The arm is involved; close-up view; the patient is a female aged 40–49: 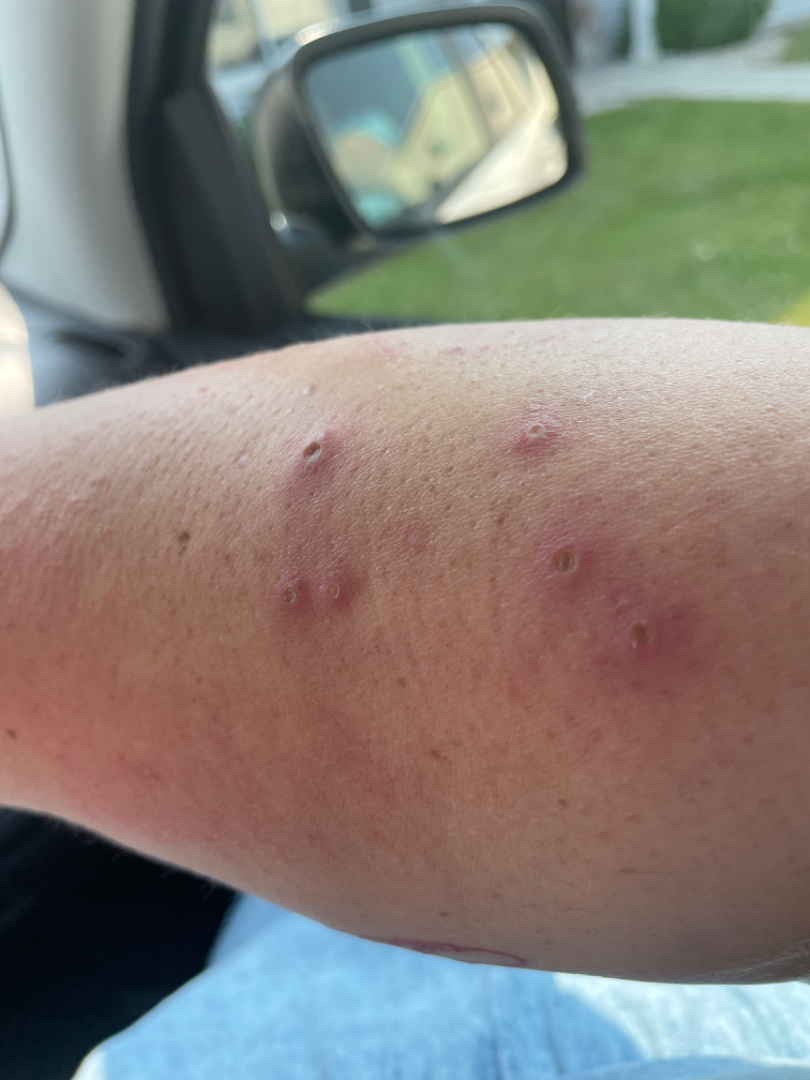Assessment:
The skin findings could not be characterized from the image.